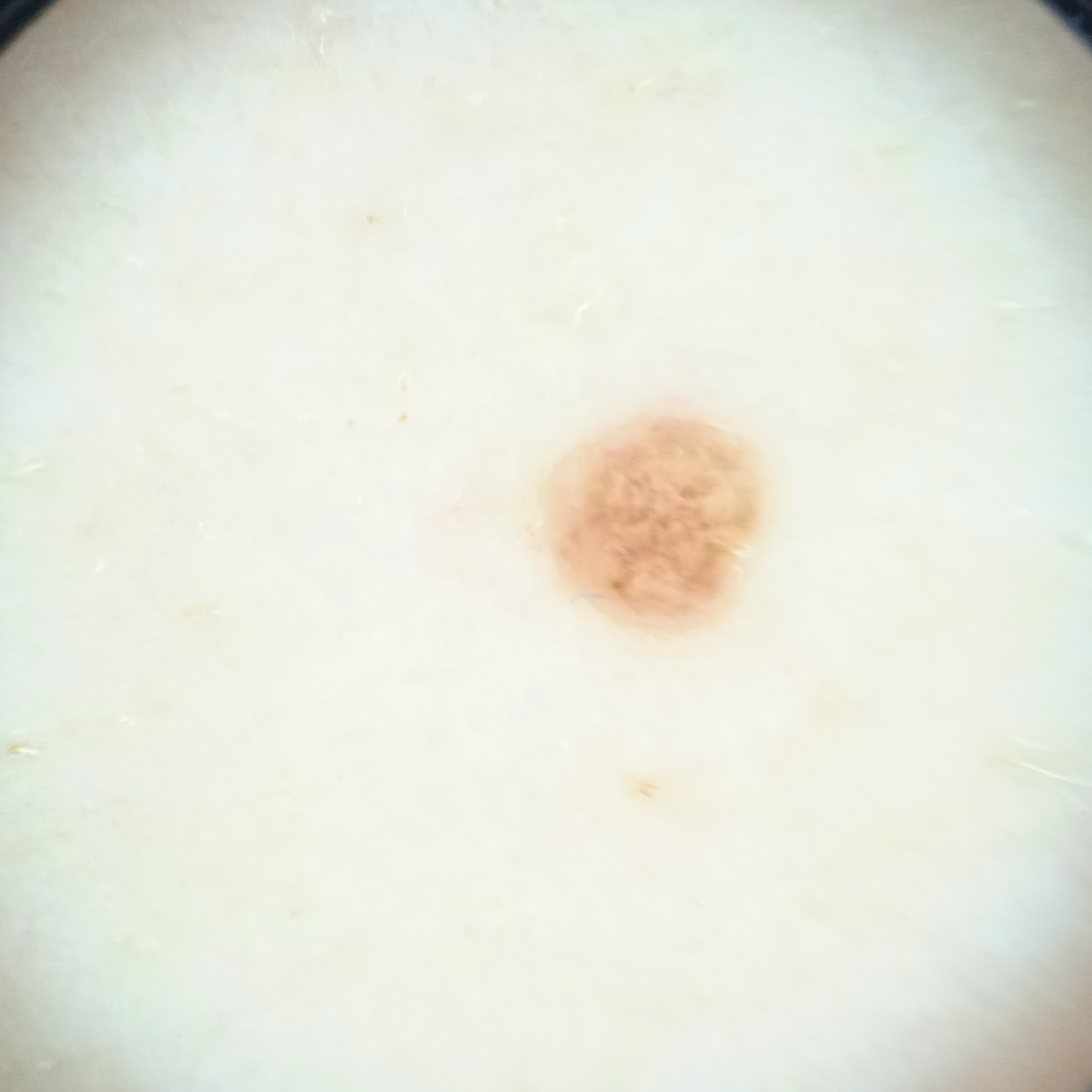The patient says their skin reddens painfully with sun exposure.
Imaged for a research study, with no referral diagnosis recorded.
On a questionnaire the patient reported no personal history of skin cancer.
Dermoscopy of a skin lesion.
A female subject 50 years of age.
A moderate number of moles by the patient's own estimate.
The lesion involves the back.
Measuring roughly 2.2 mm.
The diagnostic impression was a melanocytic nevus.